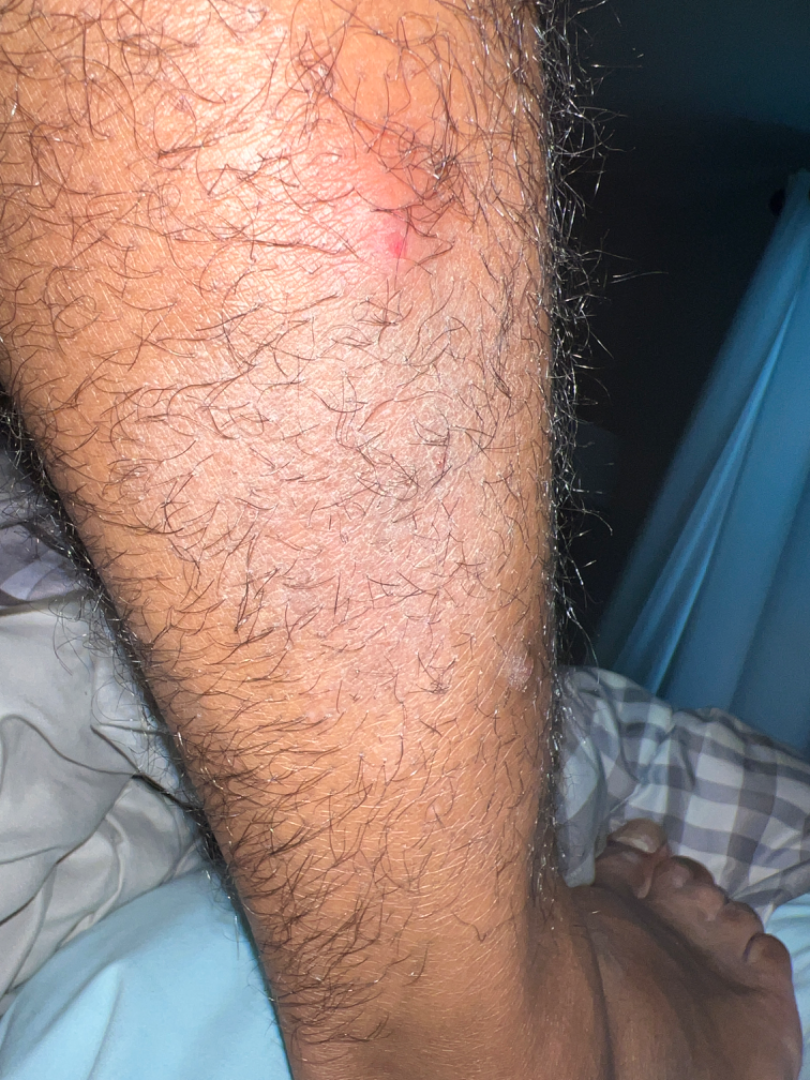The image was not sufficient for the reviewer to characterize the skin condition.
The photograph is a close-up of the affected area.
Skin tone: Fitzpatrick phototype IV; human graders estimated Monk skin tone scale 5 or 6 (two reviewer pools).